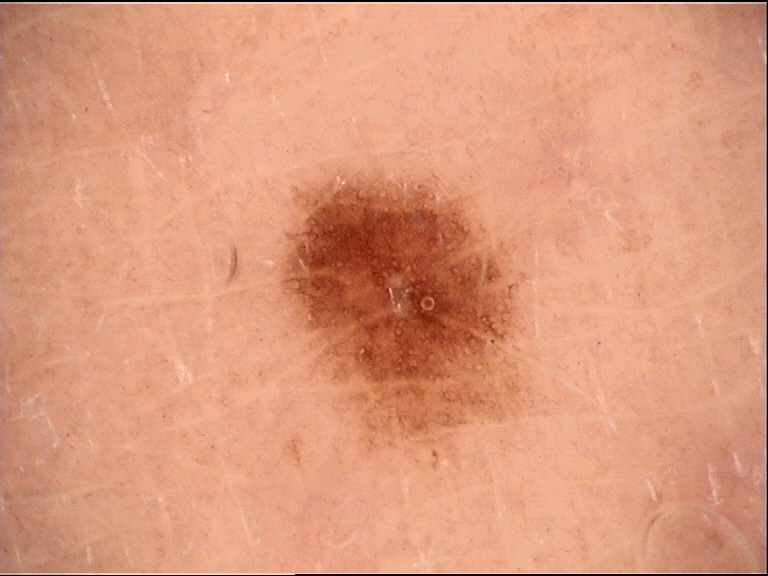Diagnosed as a dysplastic junctional nevus.